A dermoscopy image of a single skin lesion.
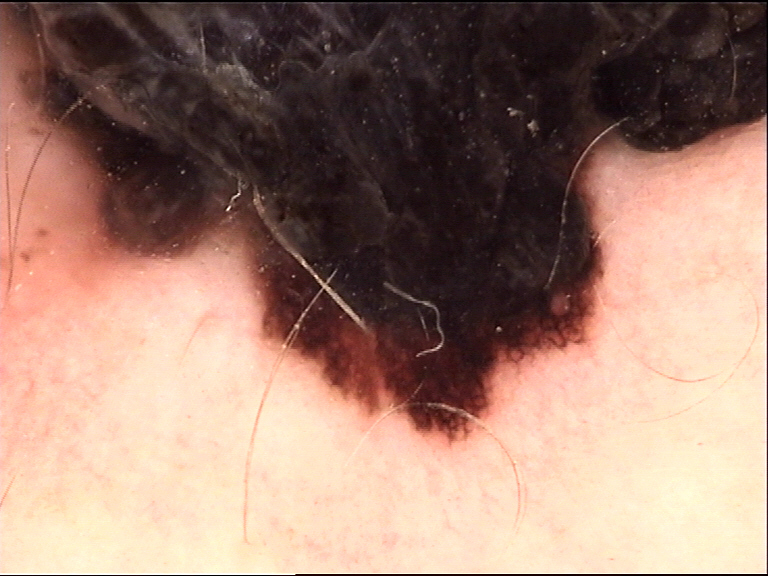- class · melanoma (biopsy-proven)